A dermoscopy image of a single skin lesion.
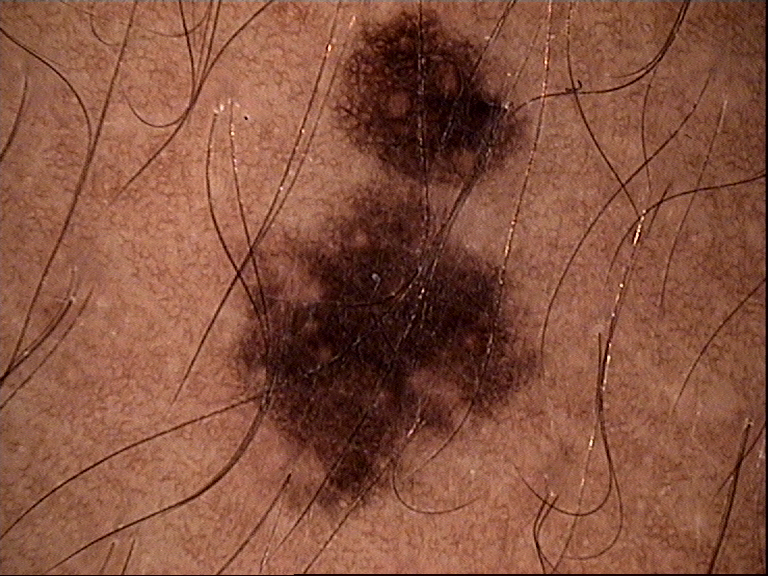{
  "diagnosis": {
    "name": "dysplastic junctional nevus",
    "code": "jd",
    "malignancy": "benign",
    "super_class": "melanocytic",
    "confirmation": "expert consensus"
  }
}